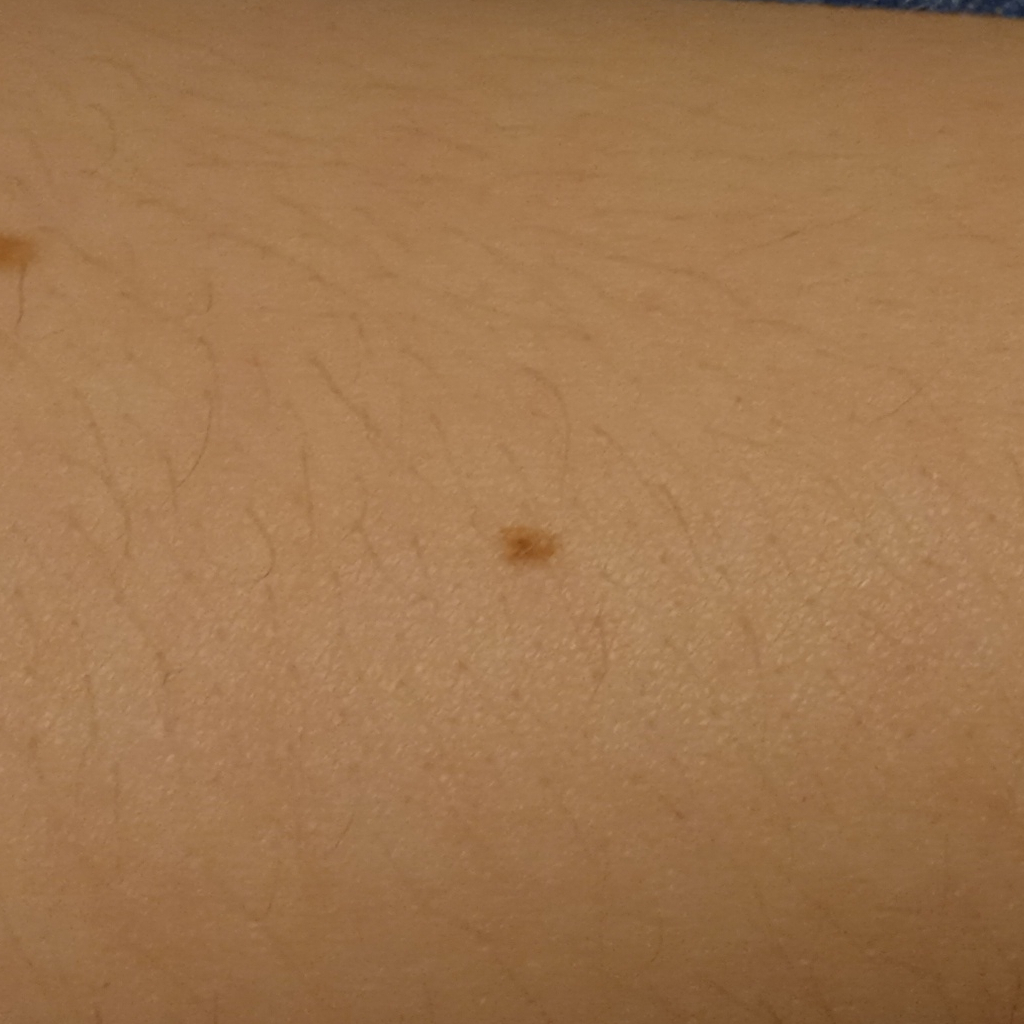clinical context: research study (no referral diagnosis) | sun reaction: skin reddens with sun exposure | subject: female, age 20 | nevus count: a moderate number of melanocytic nevi | image: clinical photo | anatomic site: an arm | size: 2.5 mm | assessment: melanocytic nevus (dermatologist consensus).